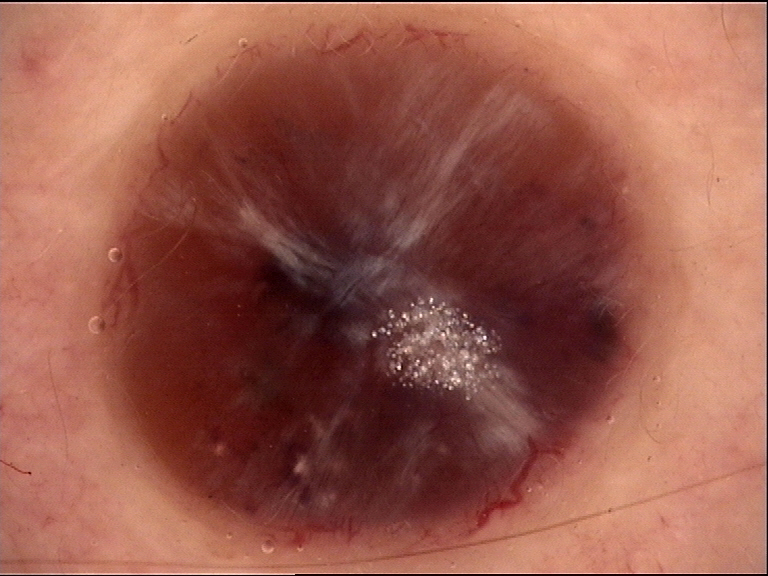class: basal cell carcinoma (biopsy-proven).